A clinical photograph of a skin lesion · history notes prior malignancy (patient or family), alcohol use, prior skin cancer (patient or family), and pesticide exposure.
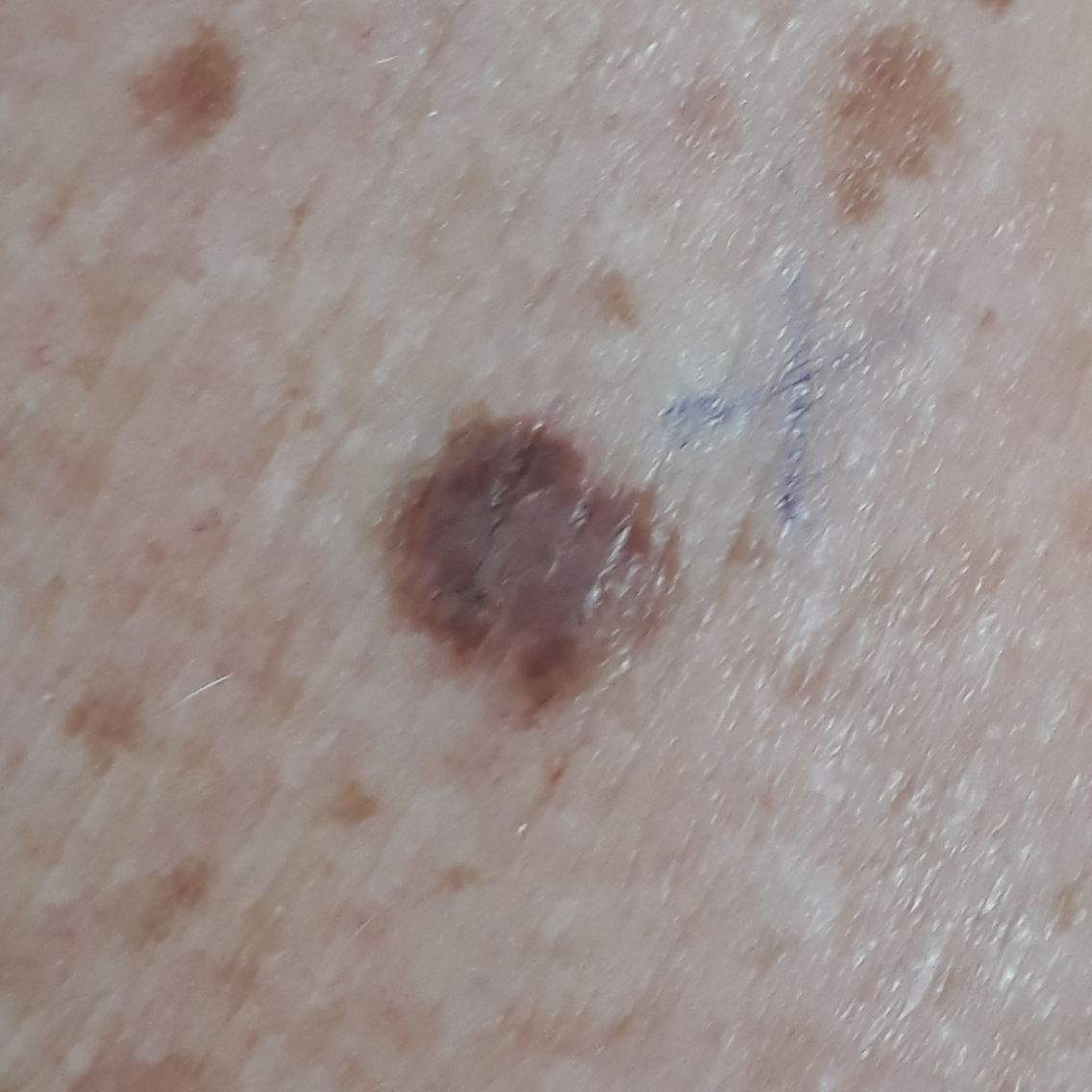location = an arm, diagnosis = nevus (biopsy-proven).